The patient was assessed as skin type II · the chart notes prior malignancy (patient or family) · a male patient 90 years of age.
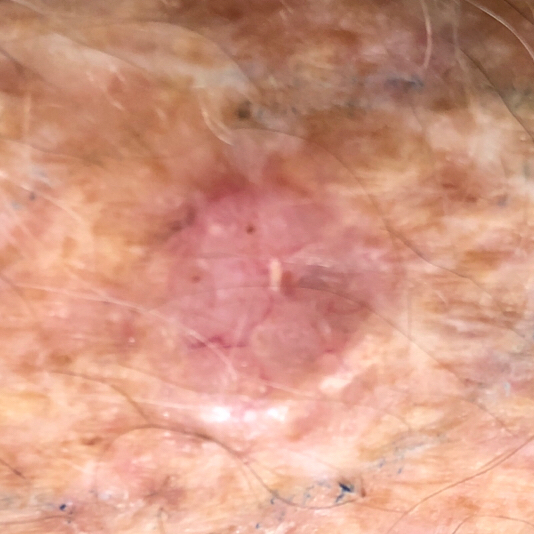– body site · a forearm
– size · 11 × 11 mm
– patient-reported symptoms · itching, growth, elevation
– diagnostic label · basal cell carcinoma (biopsy-proven)